An image taken at an angle · the contributor notes the lesion is raised or bumpy · reported lesion symptoms include itching · the lesion involves the back of the torso and front of the torso · skin tone: Fitzpatrick skin type III; non-clinician graders estimated a MST of 2 · reported duration is about one day:
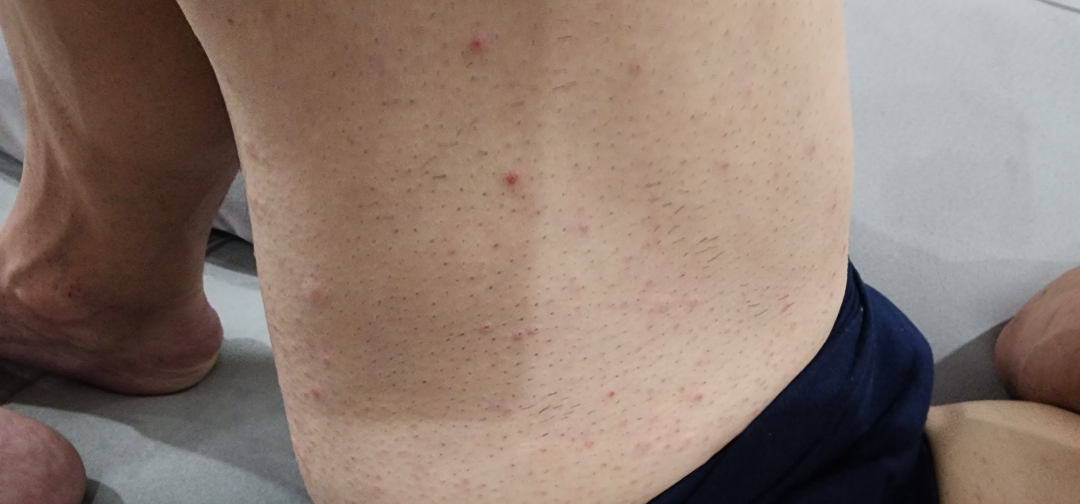Findings: Most consistent with Folliculitis.